A dermoscopy image of a single skin lesion · a male patient, aged approximately 55:
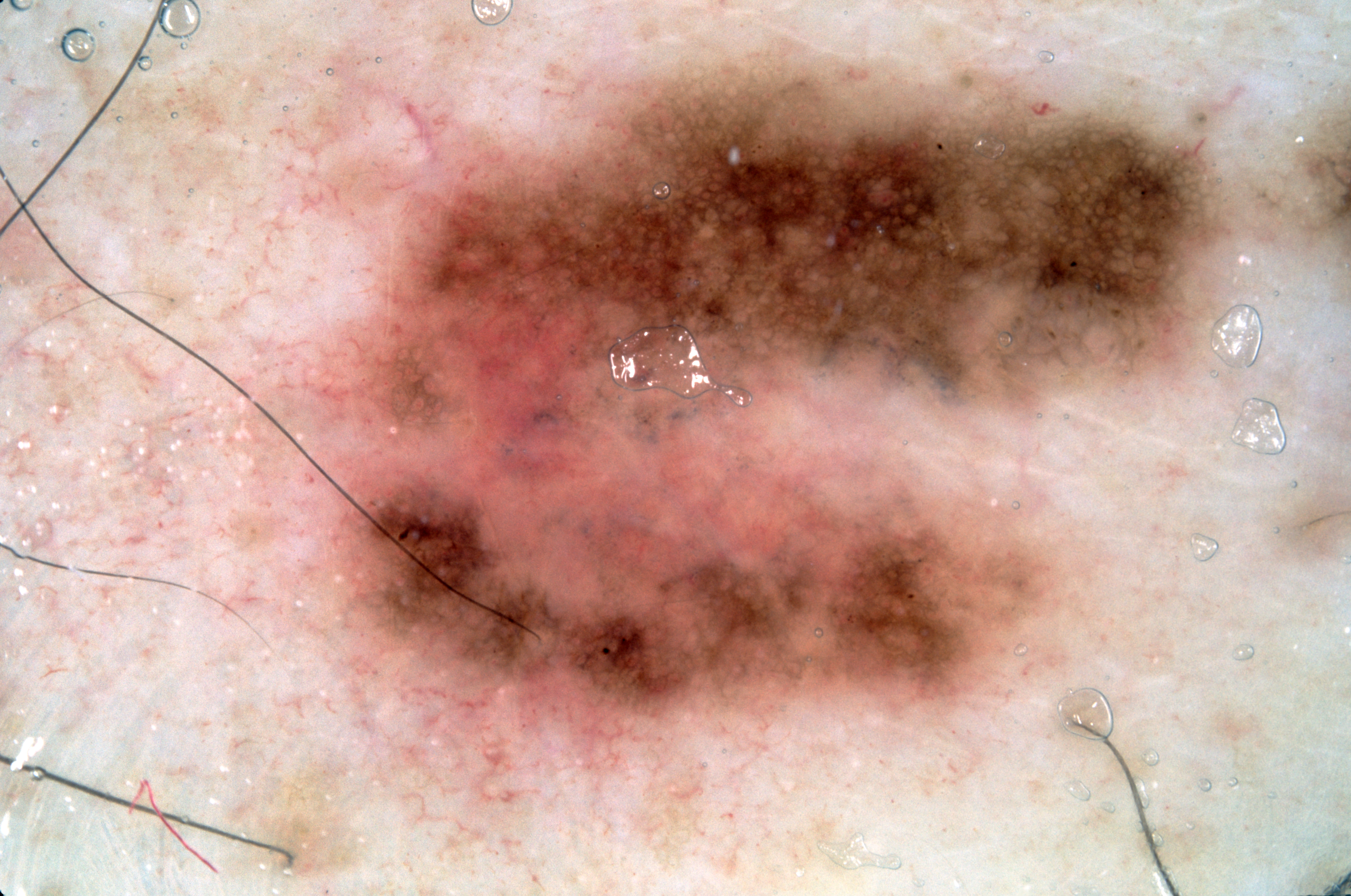Dermoscopic review identifies pigment network and milia-like cysts. The lesion's extent is x1=296, y1=56, x2=1224, y2=770. On biopsy, the diagnosis was a melanoma, a malignant lesion.